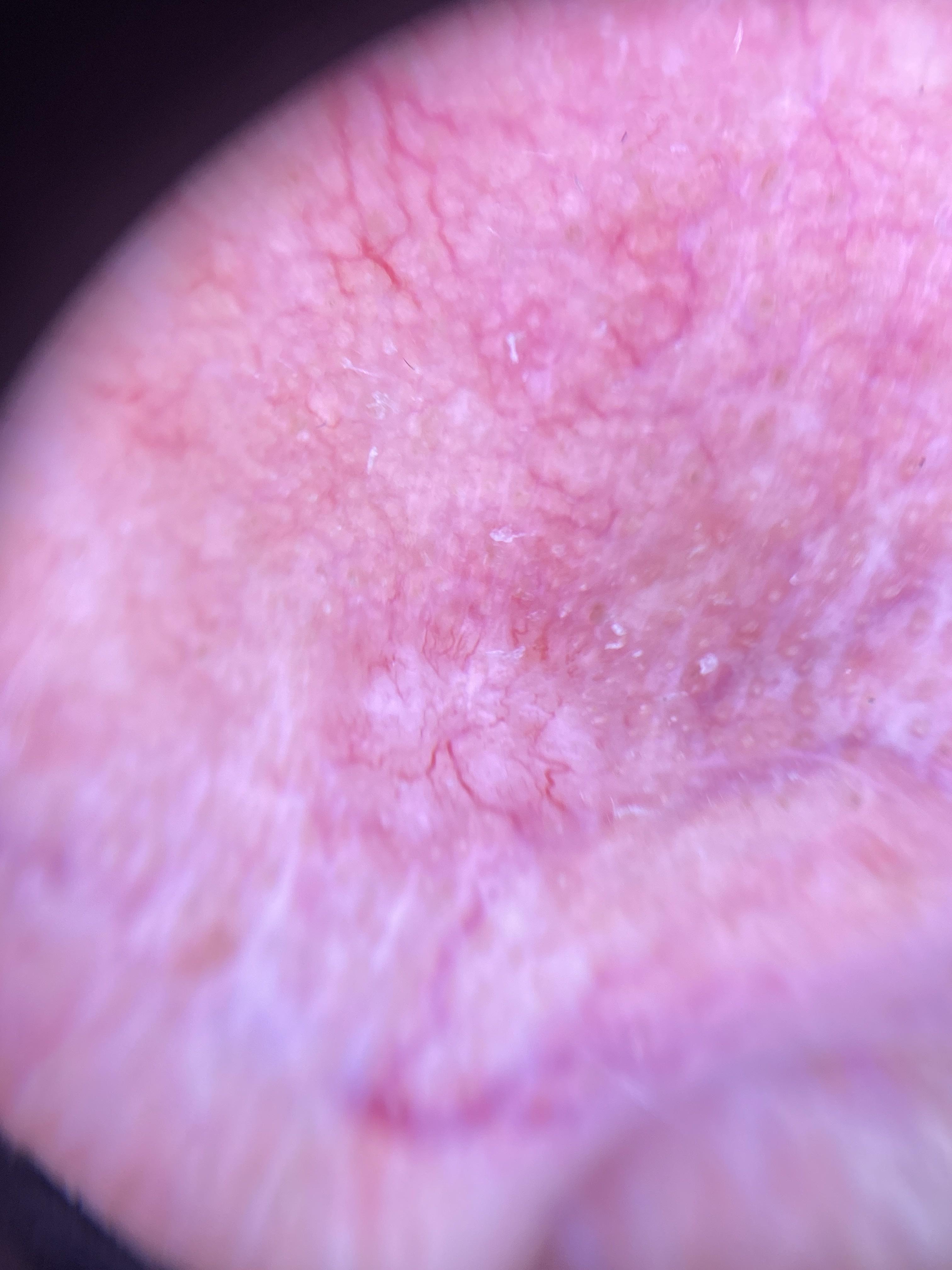skin phototype: II
imaging: contact-polarized dermoscopy
subject: male, aged around 80
melanoma history: a previous melanoma
body site: the head or neck
pathology: Basal cell carcinoma (biopsy-proven)